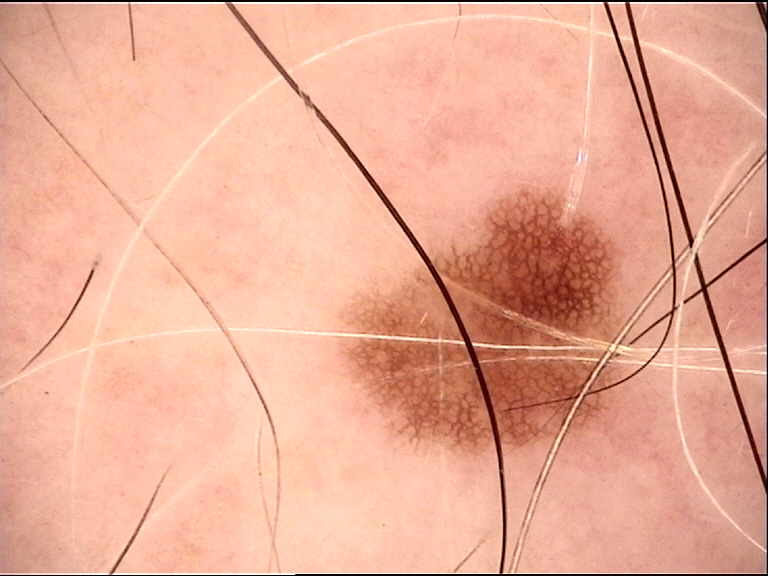A skin lesion imaged with a dermatoscope.
Classified as a benign lesion — a dysplastic junctional nevus.